A dermoscopic photograph of a skin lesion.
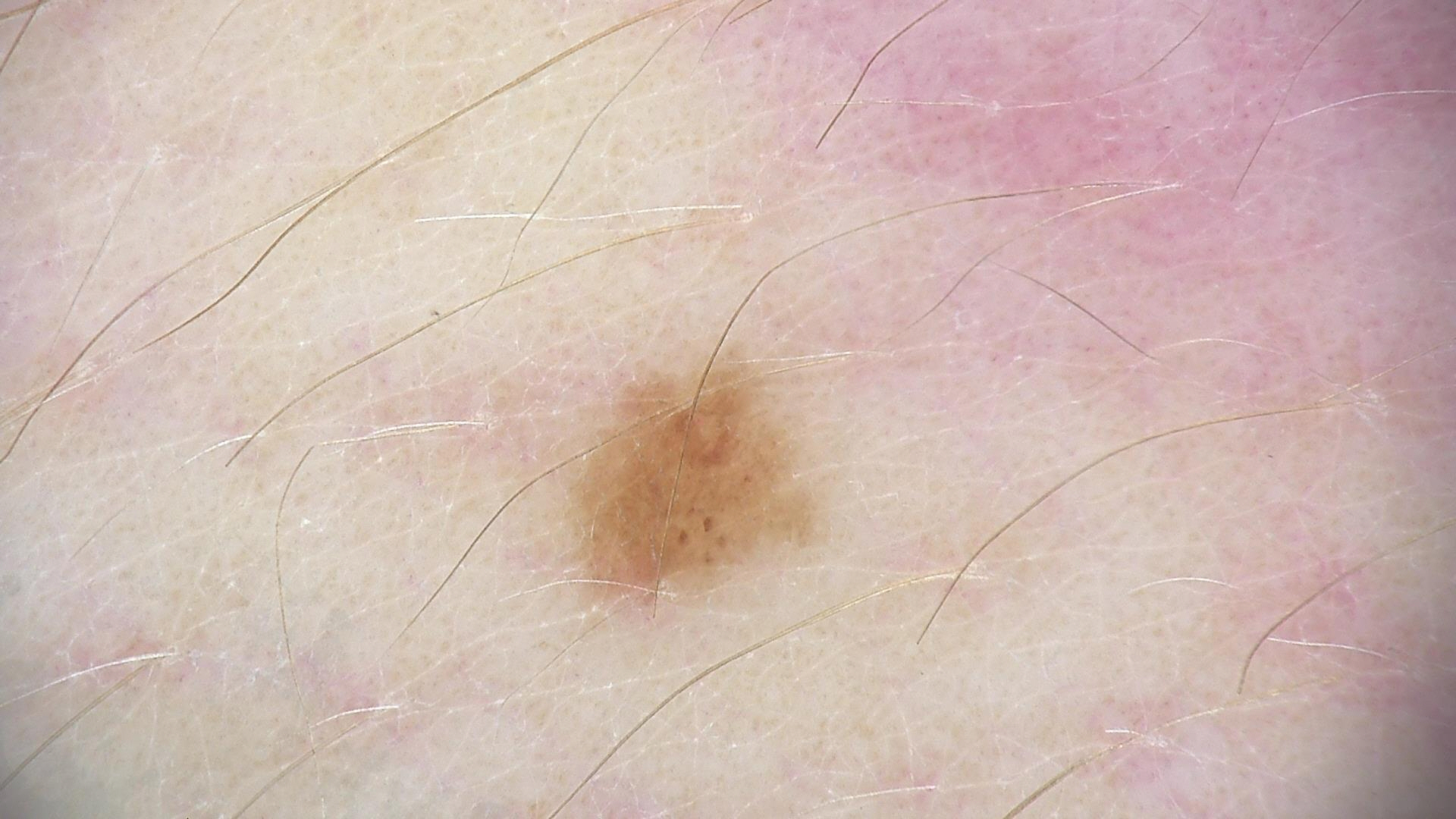Case:
– label · dysplastic junctional nevus (expert consensus)